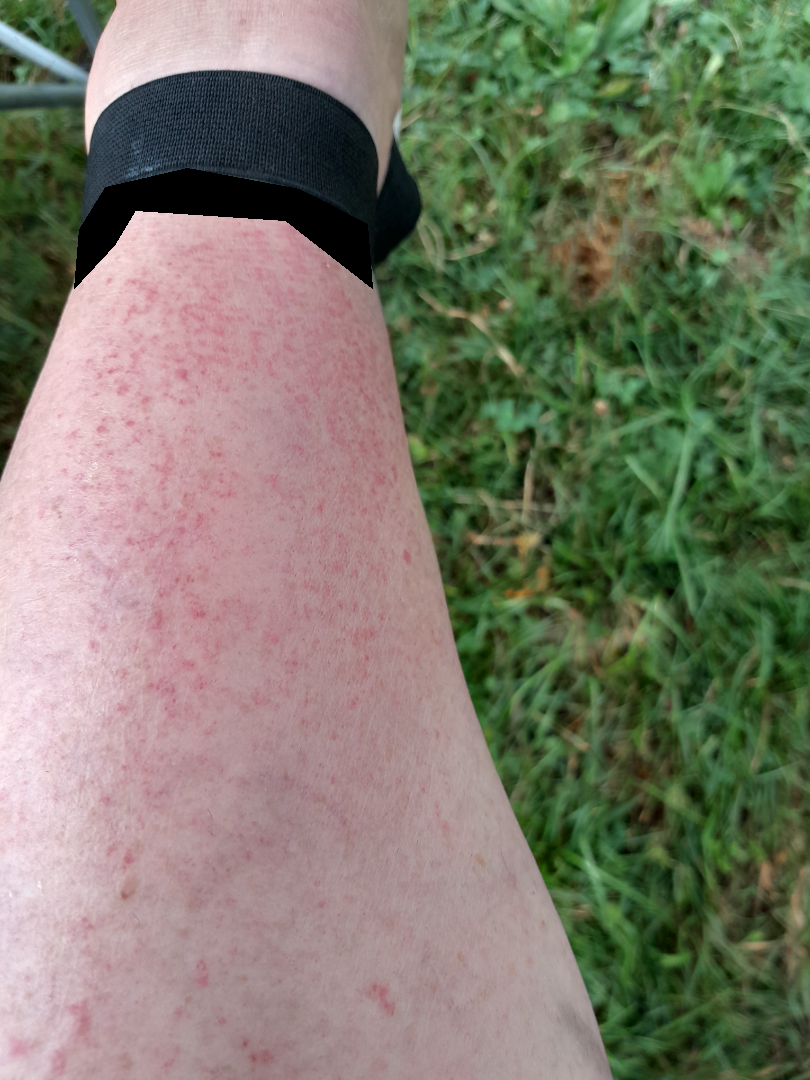assessment = indeterminate